A skin lesion imaged with a dermatoscope.
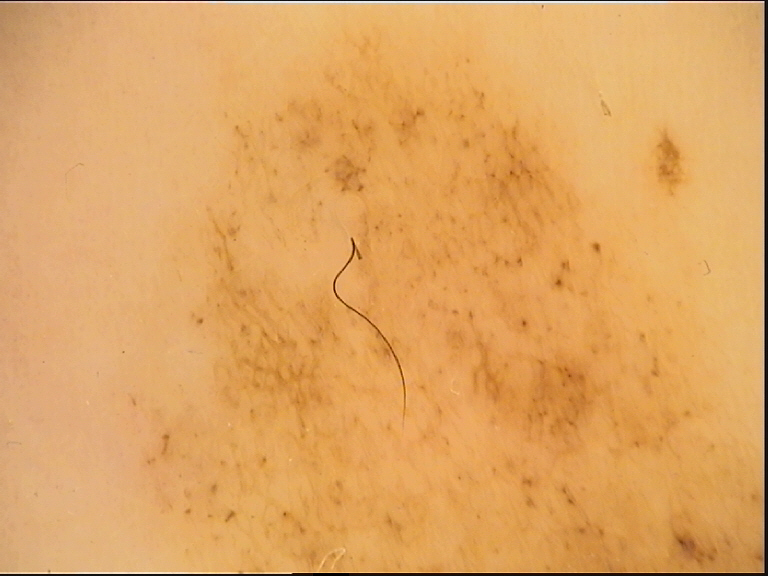Findings:
The architecture is that of a banal lesion.
Conclusion:
Consistent with a congenital junctional nevus.